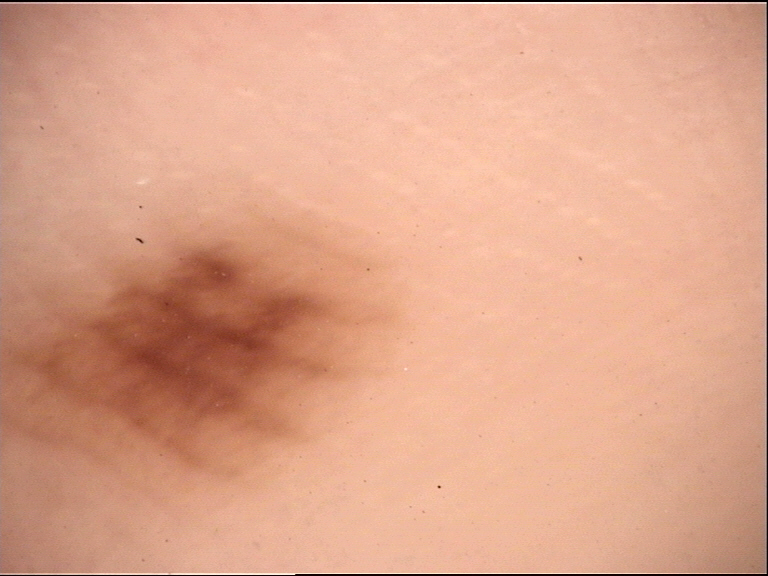Conclusion:
Diagnosed as an acral junctional nevus.